A skin lesion imaged with a dermatoscope.
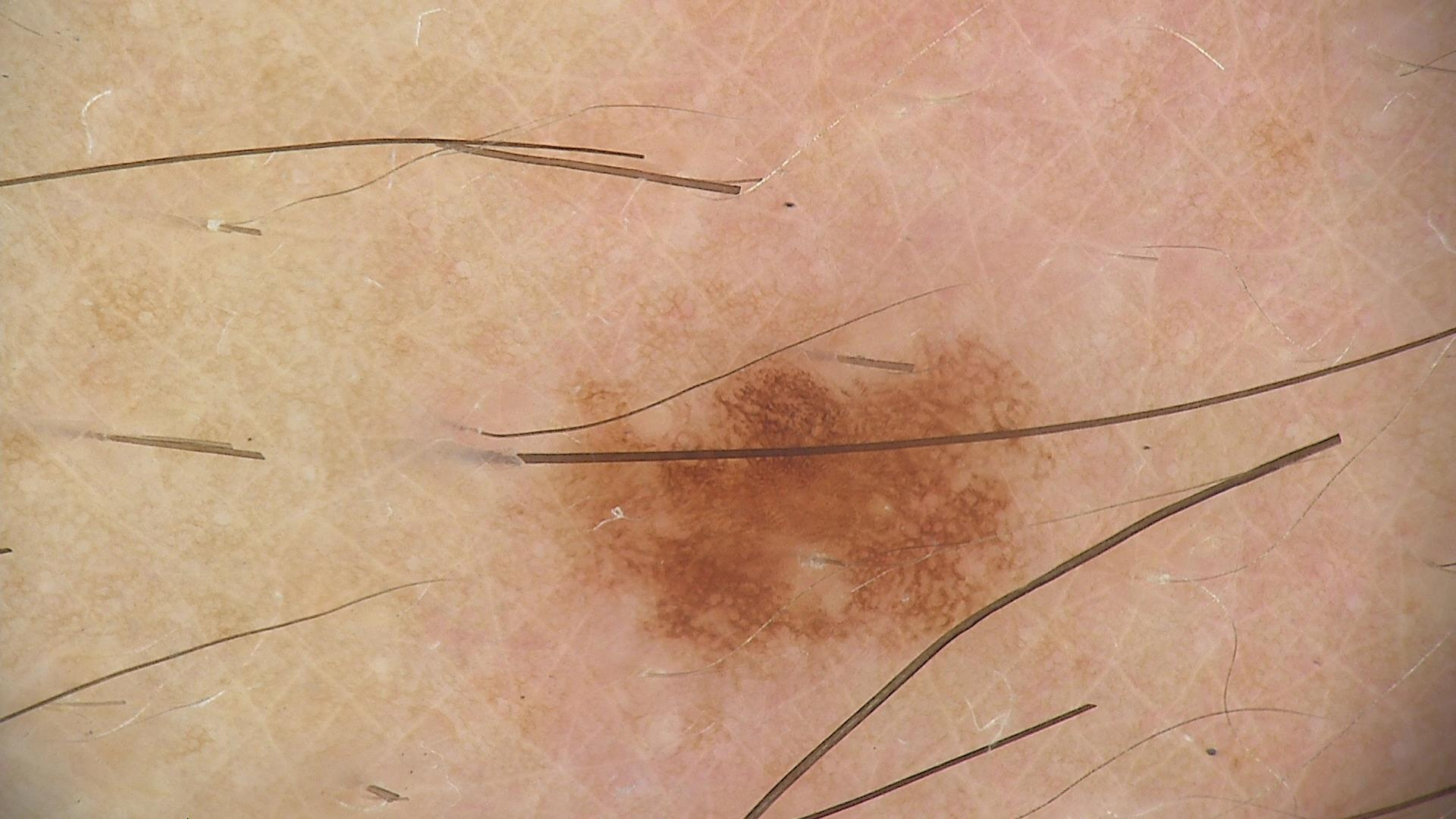Conclusion: Classified as a dysplastic junctional nevus.